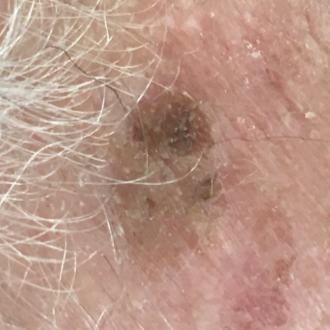Notes:
• imaging · smartphone clinical photo
• subject · 86 years old
• site · the face
• reported symptoms · elevation / no pain, no growth
• assessment · seborrheic keratosis (clinical consensus)